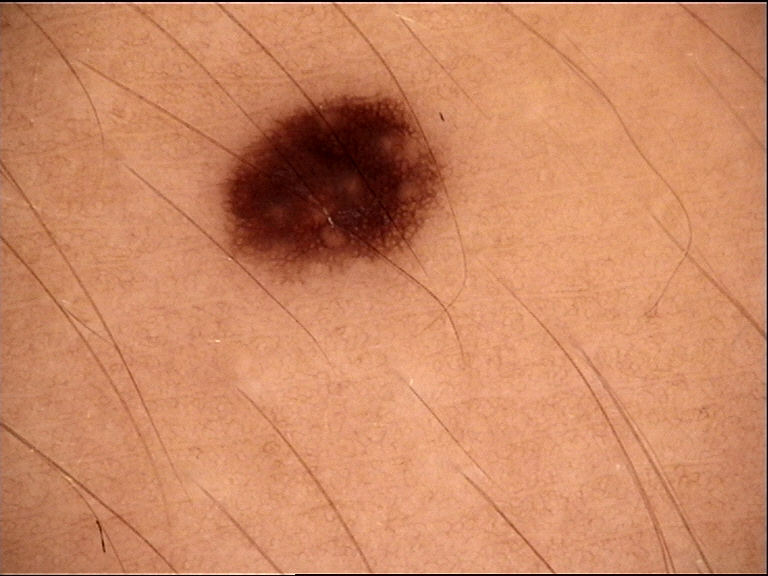Summary:
Dermoscopy of a skin lesion.
Conclusion:
The diagnosis was a banal lesion — a junctional nevus.